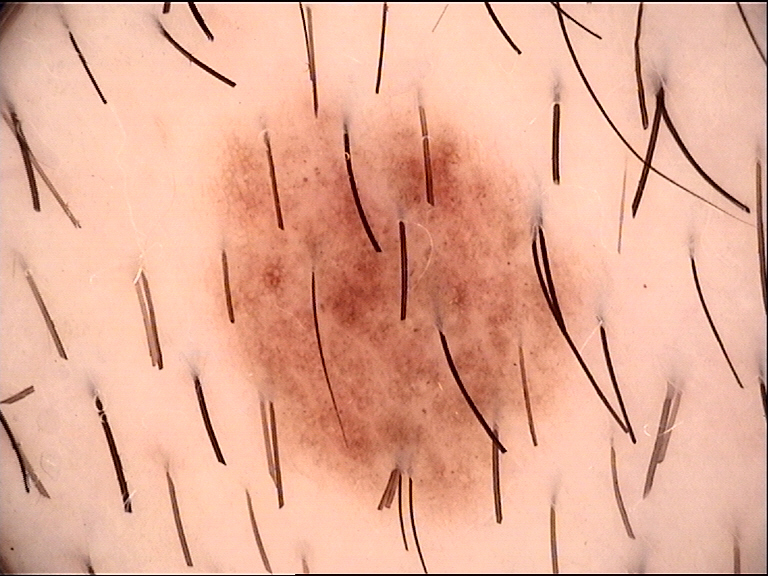<dermoscopy>
  <diagnosis>
    <name>dysplastic compound nevus</name>
    <code>cd</code>
    <malignancy>benign</malignancy>
    <super_class>melanocytic</super_class>
    <confirmation>expert consensus</confirmation>
  </diagnosis>
</dermoscopy>